Close-up view. Fitzpatrick phototype V; human graders estimated Monk Skin Tone 6.
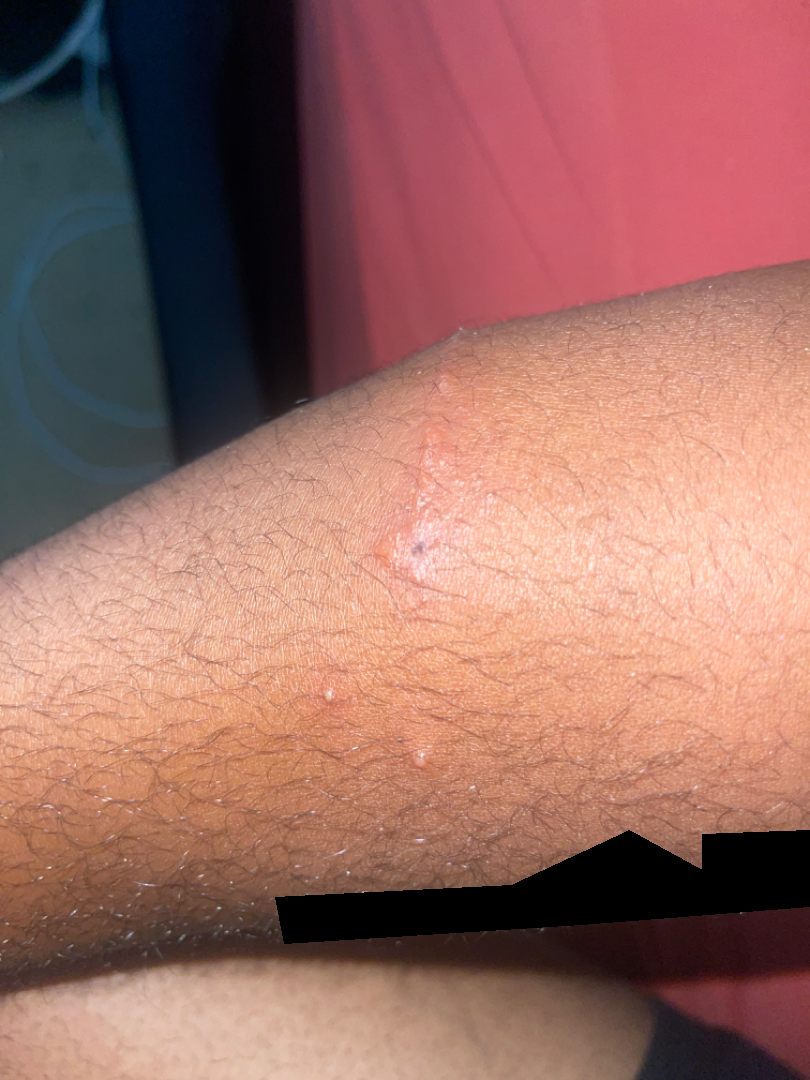assessment — the differential is split between Acute dermatitis, NOS; Contact dermatitis caused by Rhus diversiloba; and Allergic Contact Dermatitis